Contact-polarized dermoscopy of a skin lesion — 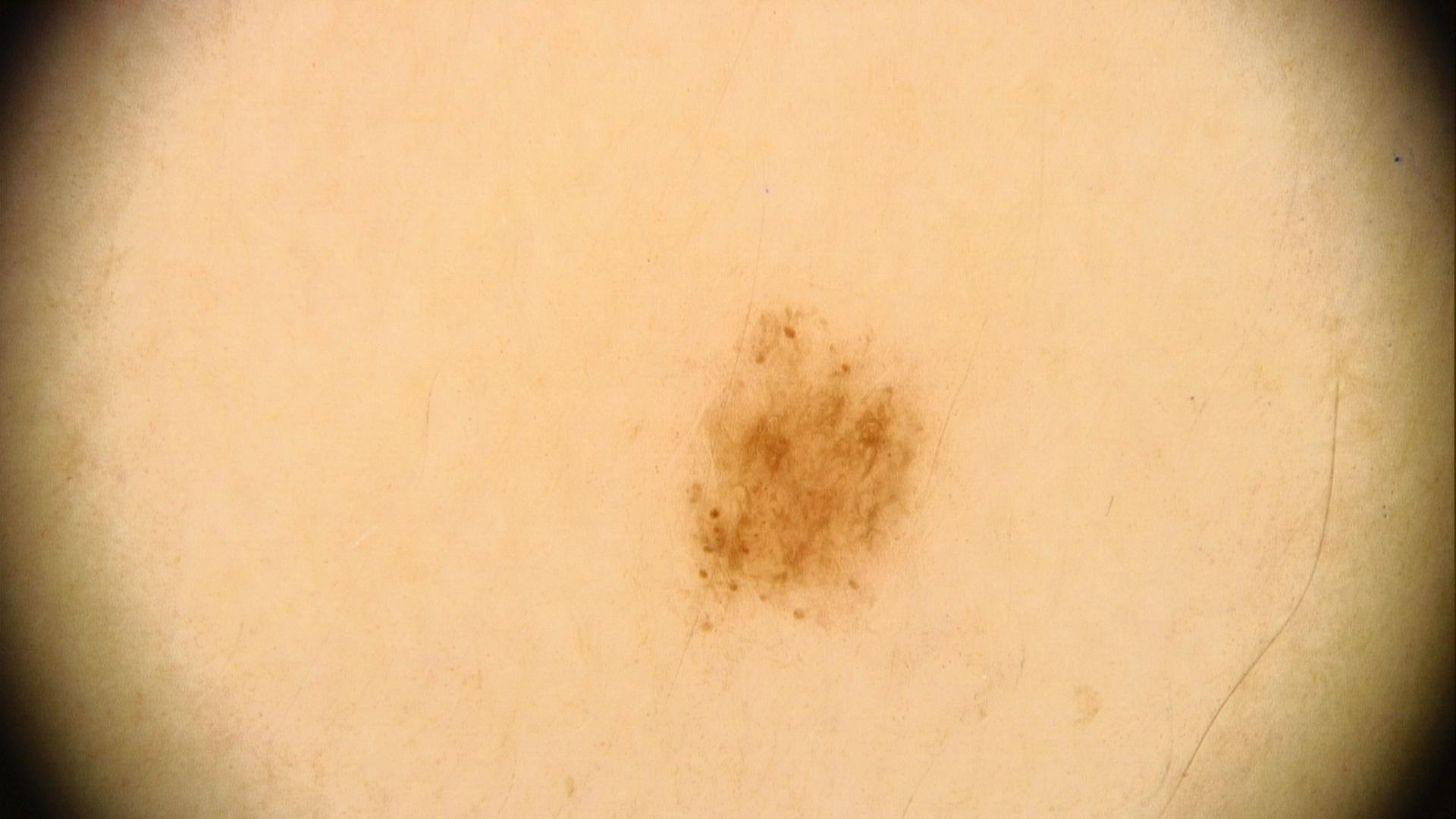Case:
* anatomic site · the trunk, specifically the anterior trunk
* impression · Nevus